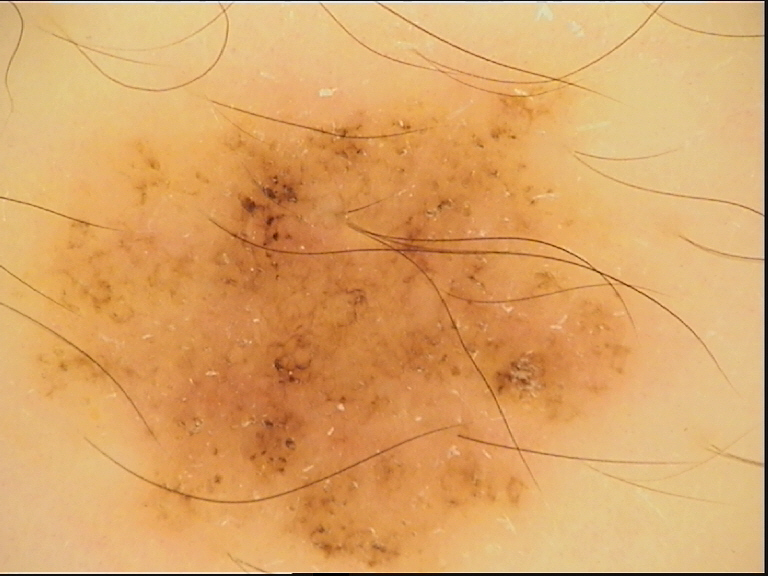A skin lesion imaged with a dermatoscope. The diagnostic label was a dysplastic junctional nevus.